Close-up view:
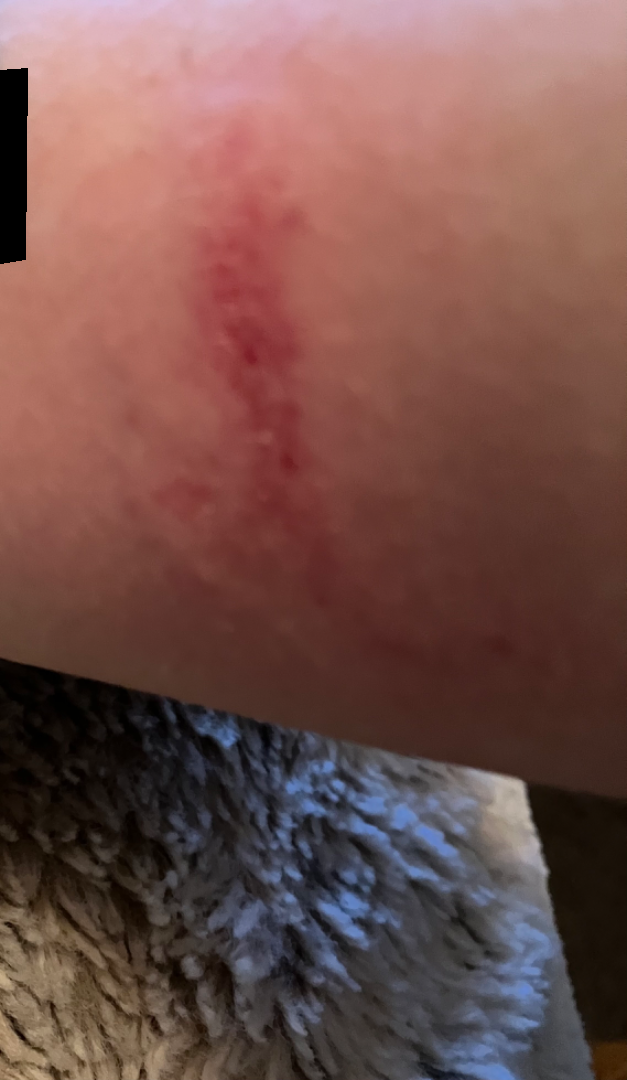The differential is split between Abrasion, scrape, or scab; Eczema; and Allergic Contact Dermatitis.